The contributor is 40–49, female. The arm, palm, back of the hand, head or neck and leg are involved. The photo was captured at an angle: 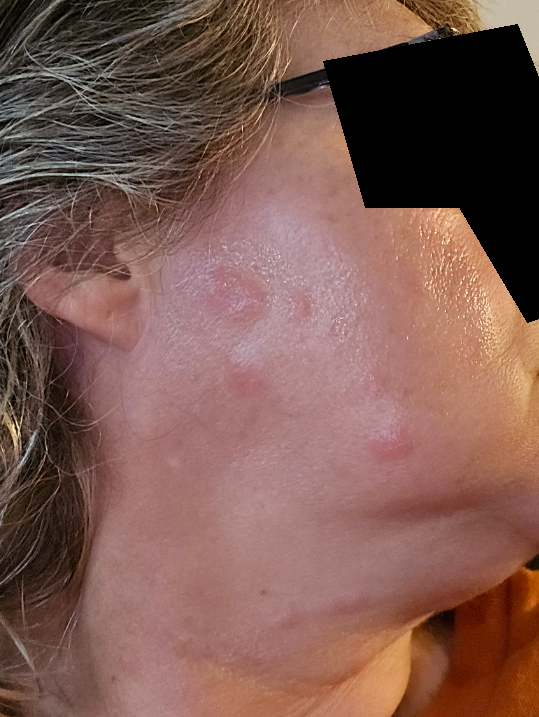Impression: The skin condition could not be confidently assessed from this image. History: Self-categorized by the patient as a rash. Reported lesion symptoms include itching and enlargement. Present for less than one week.